A skin lesion imaged with a dermatoscope.
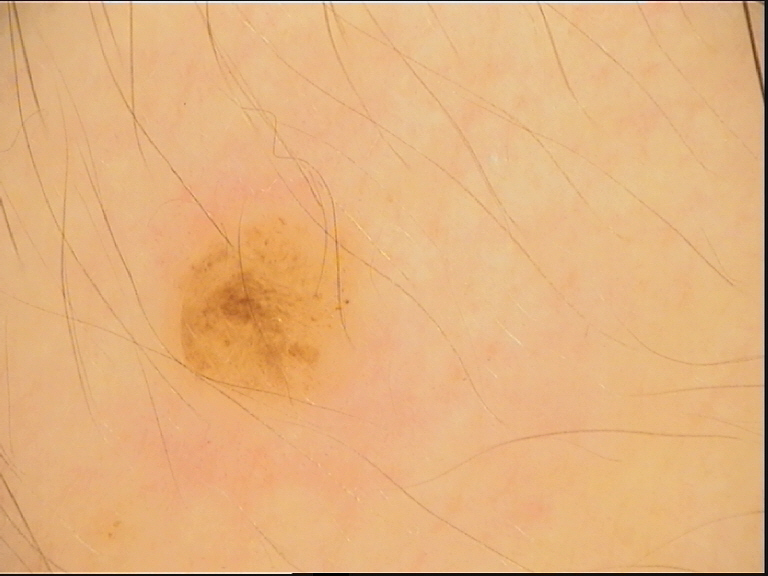category = banal; label = compound nevus (expert consensus).